The lesion involves the arm, leg and back of the torso. The photograph was taken at a distance. Self-reported Fitzpatrick phototype V; non-clinician graders estimated Monk skin tone scale 1 or 2. The contributor is 30–39, male. The condition has been present for less than one week. Symptoms reported: itching. The patient described the issue as a rash: 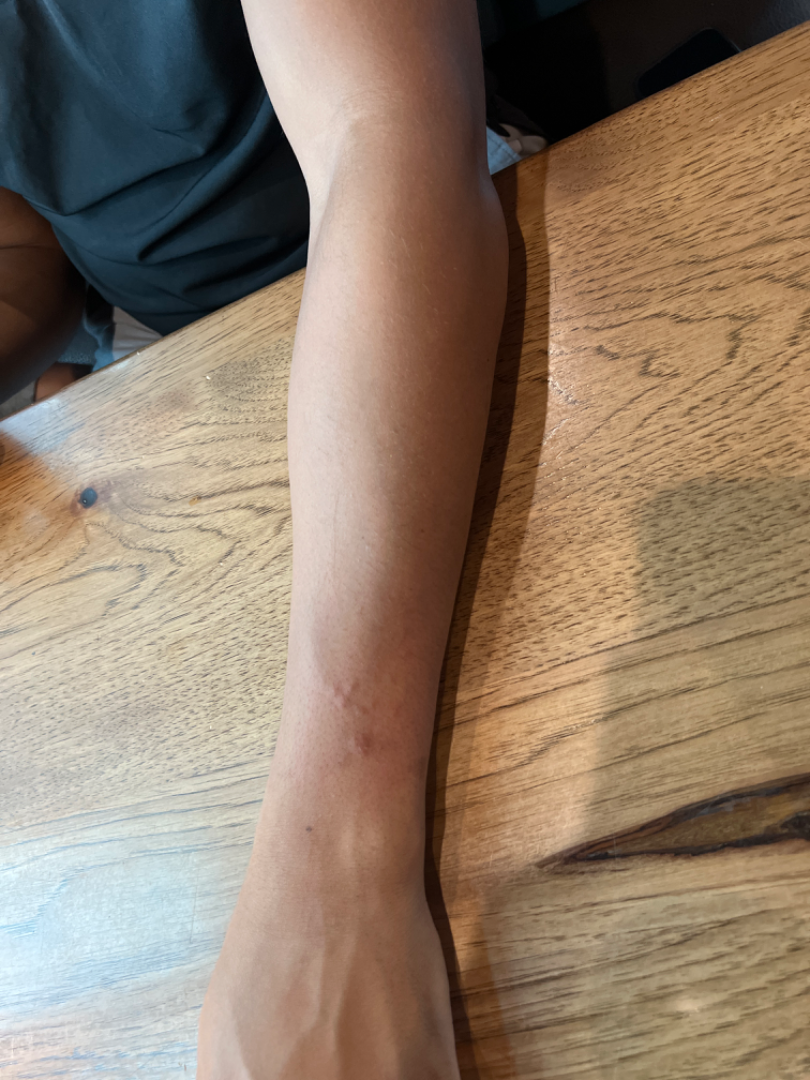Q: What was the assessment?
A: unable to determine